A dermoscopy image of a single skin lesion.
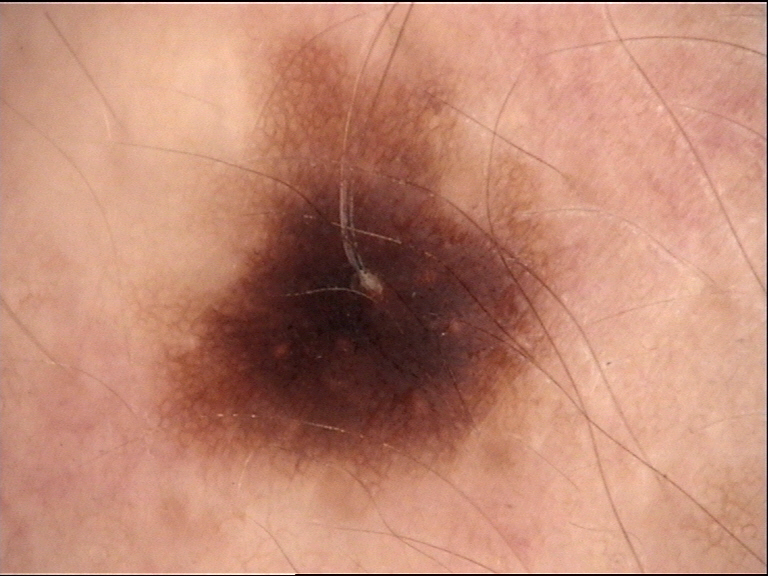classification: banal | label: junctional nevus (expert consensus).